The photo was captured at an angle.
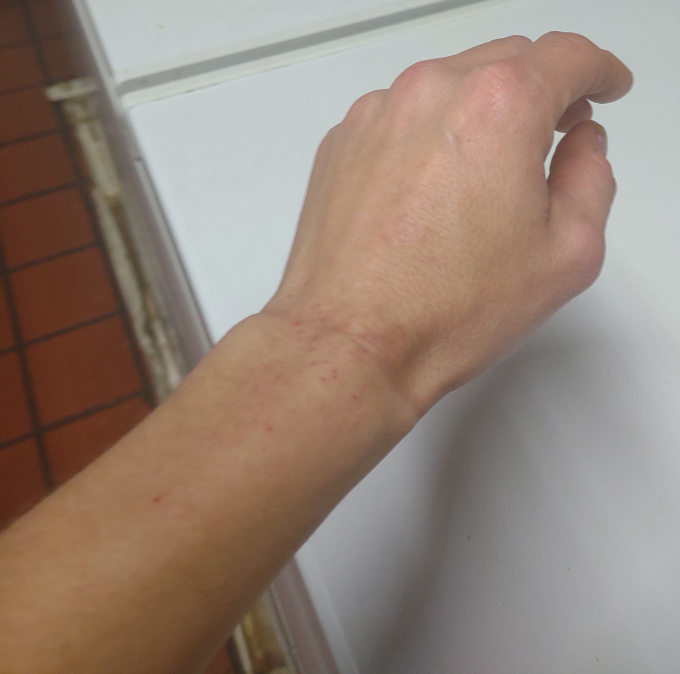Findings: No differential diagnosis could be assigned on photographic review.